A clinical photograph showing a skin lesion; a male subject 72 years of age; imaged for a research study, with no referral diagnosis recorded:
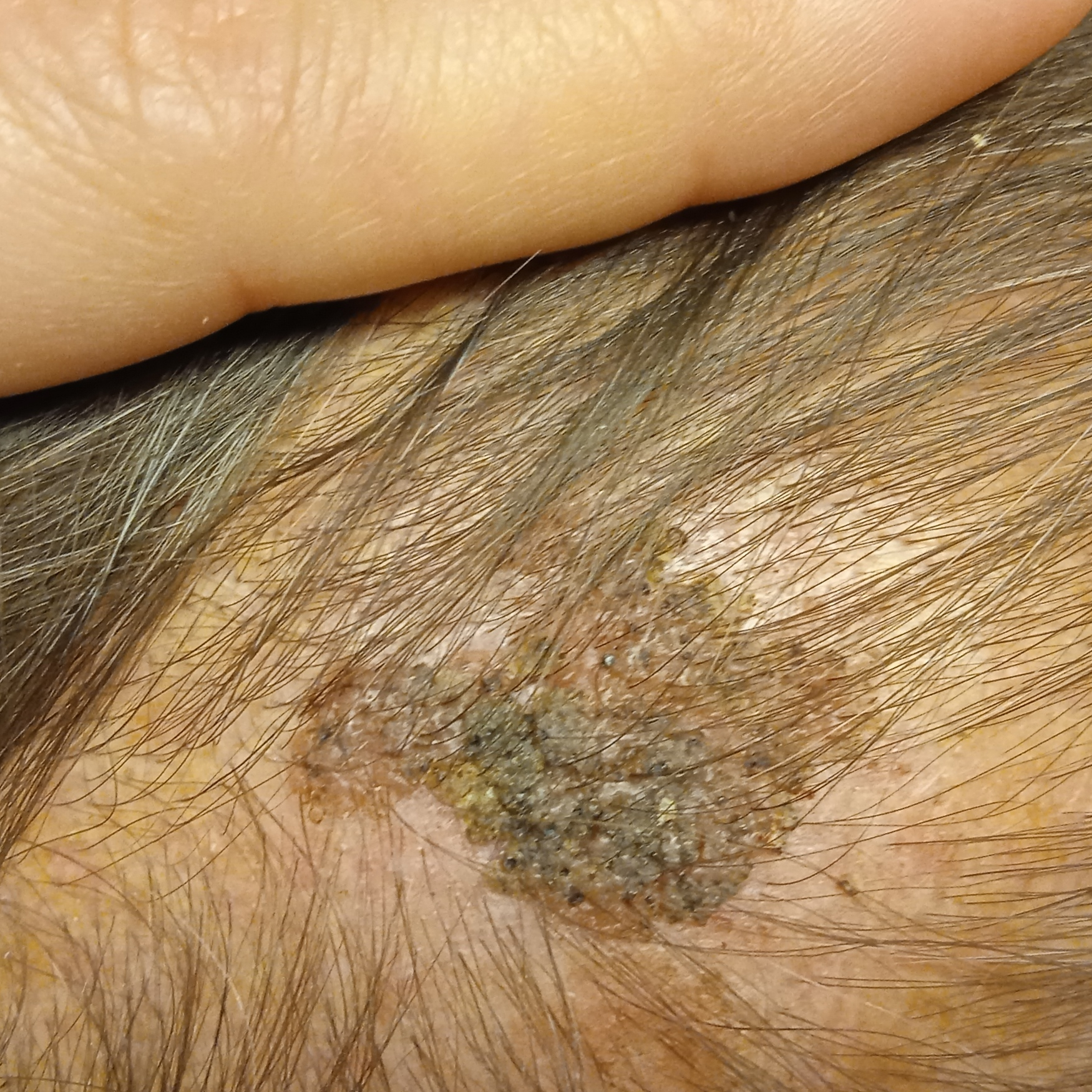The lesion is on the head. The lesion is about 19.2 mm across. The dermatologists' assessment was a seborrheic keratosis.